The photo was captured at an angle — 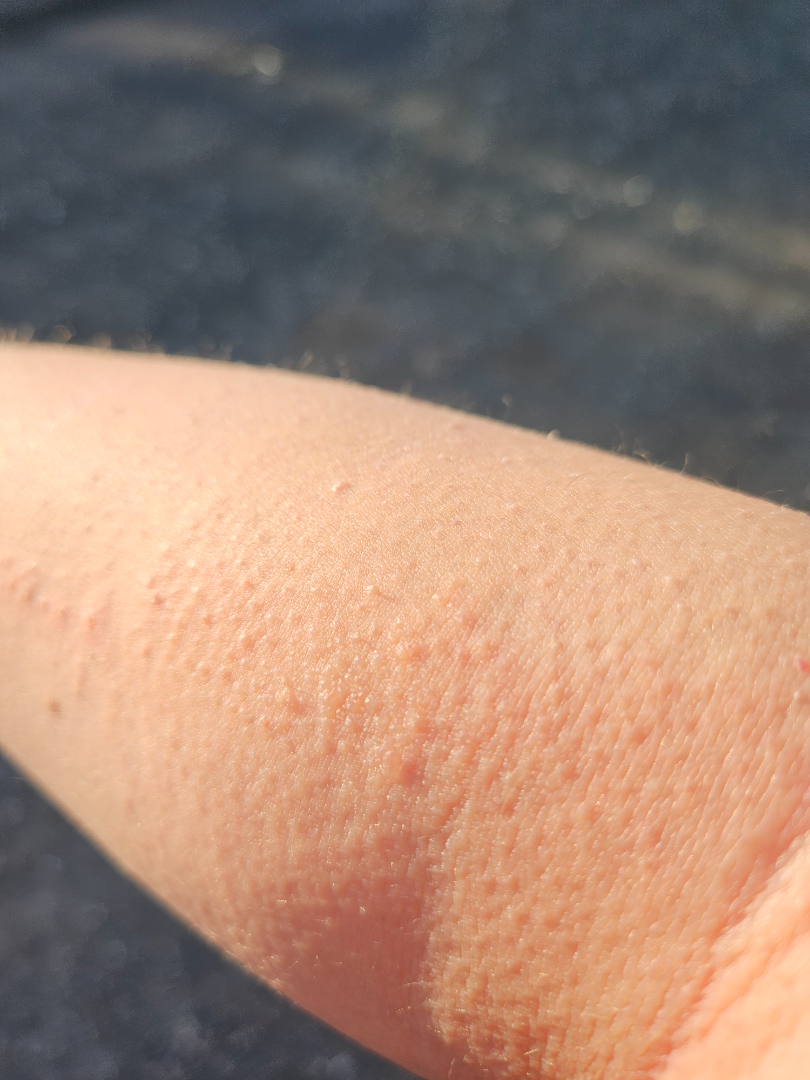{"differential": {"tied_lead": ["Keratosis pilaris", "Eczema", "Allergic Contact Dermatitis"]}}